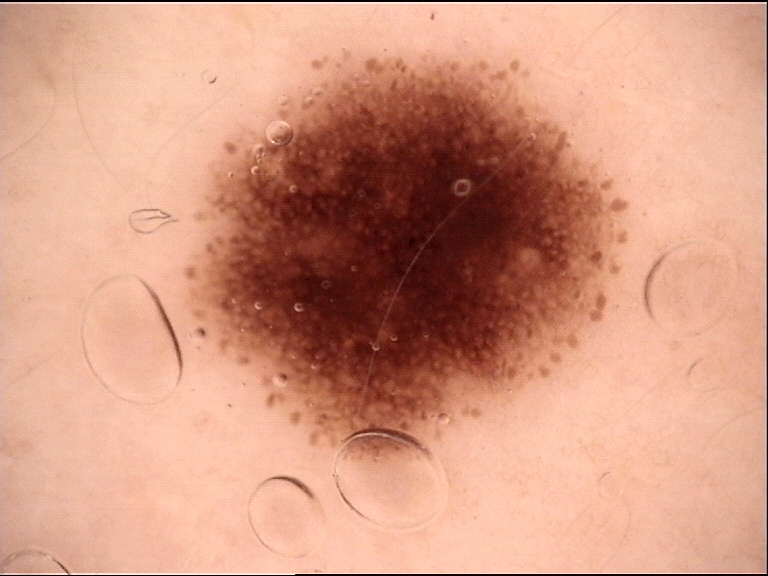Summary:
Dermoscopy of a skin lesion.
Conclusion:
Classified as a dysplastic junctional nevus.